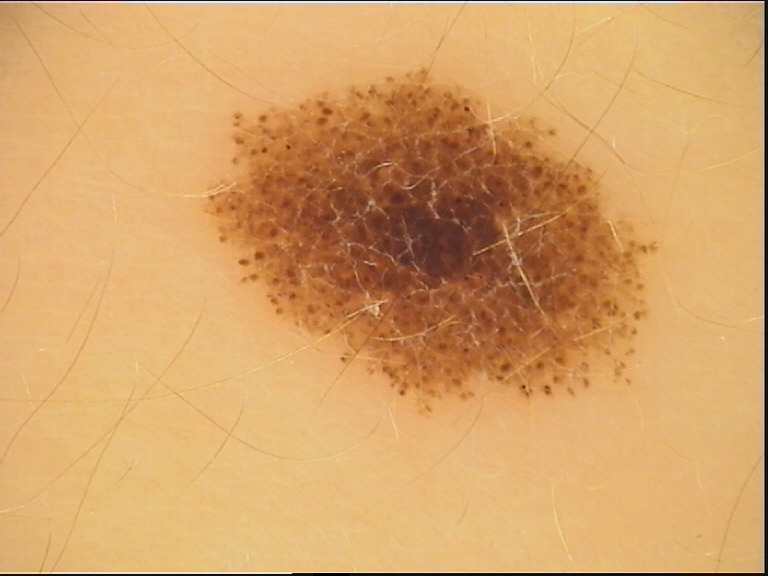A skin lesion imaged with a dermatoscope. Diagnosed as a benign lesion — a dysplastic compound nevus.